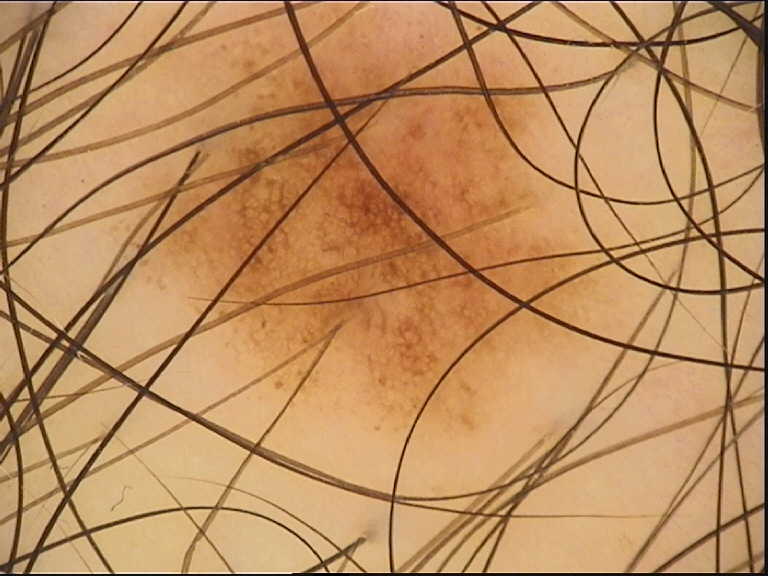image: dermoscopy
diagnosis:
  name: dysplastic junctional nevus
  code: jd
  malignancy: benign
  super_class: melanocytic
  confirmation: expert consensus